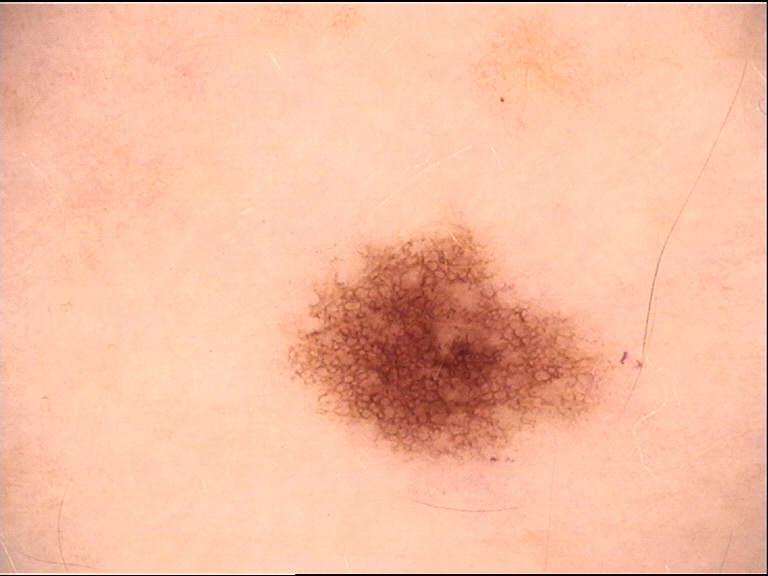Impression: The diagnostic label was a dysplastic junctional nevus.